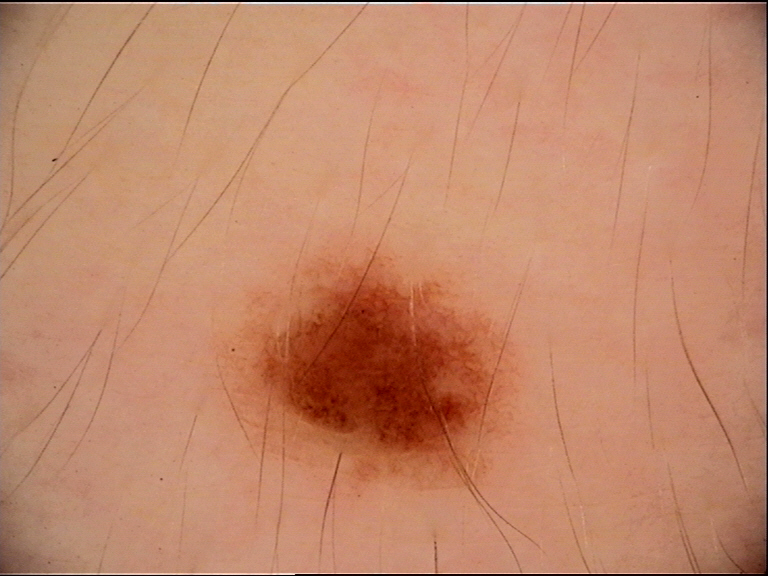Labeled as a benign lesion — a dysplastic junctional nevus.